Dermoscopy of a skin lesion: 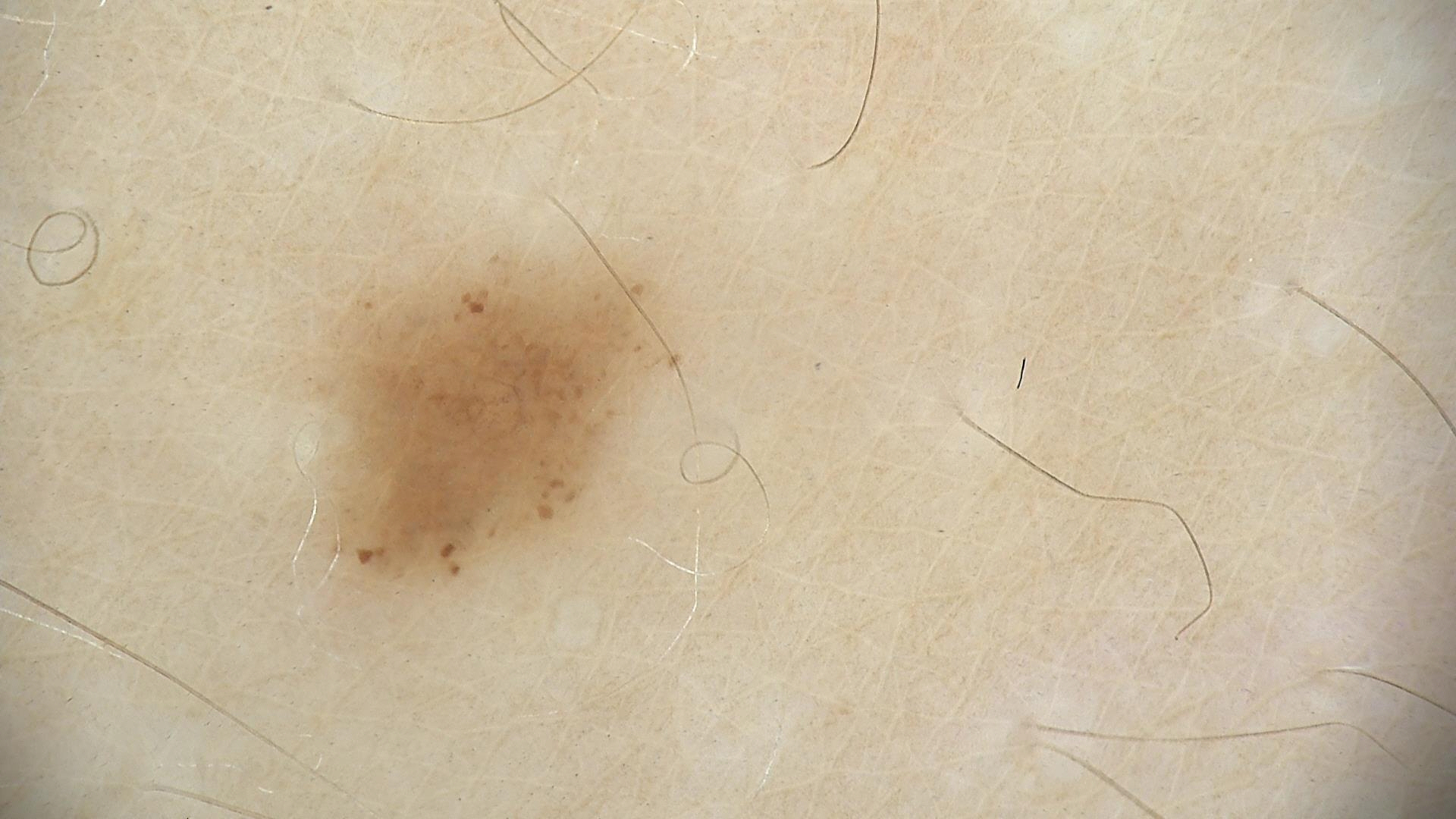Consistent with a benign lesion — a dysplastic junctional nevus.